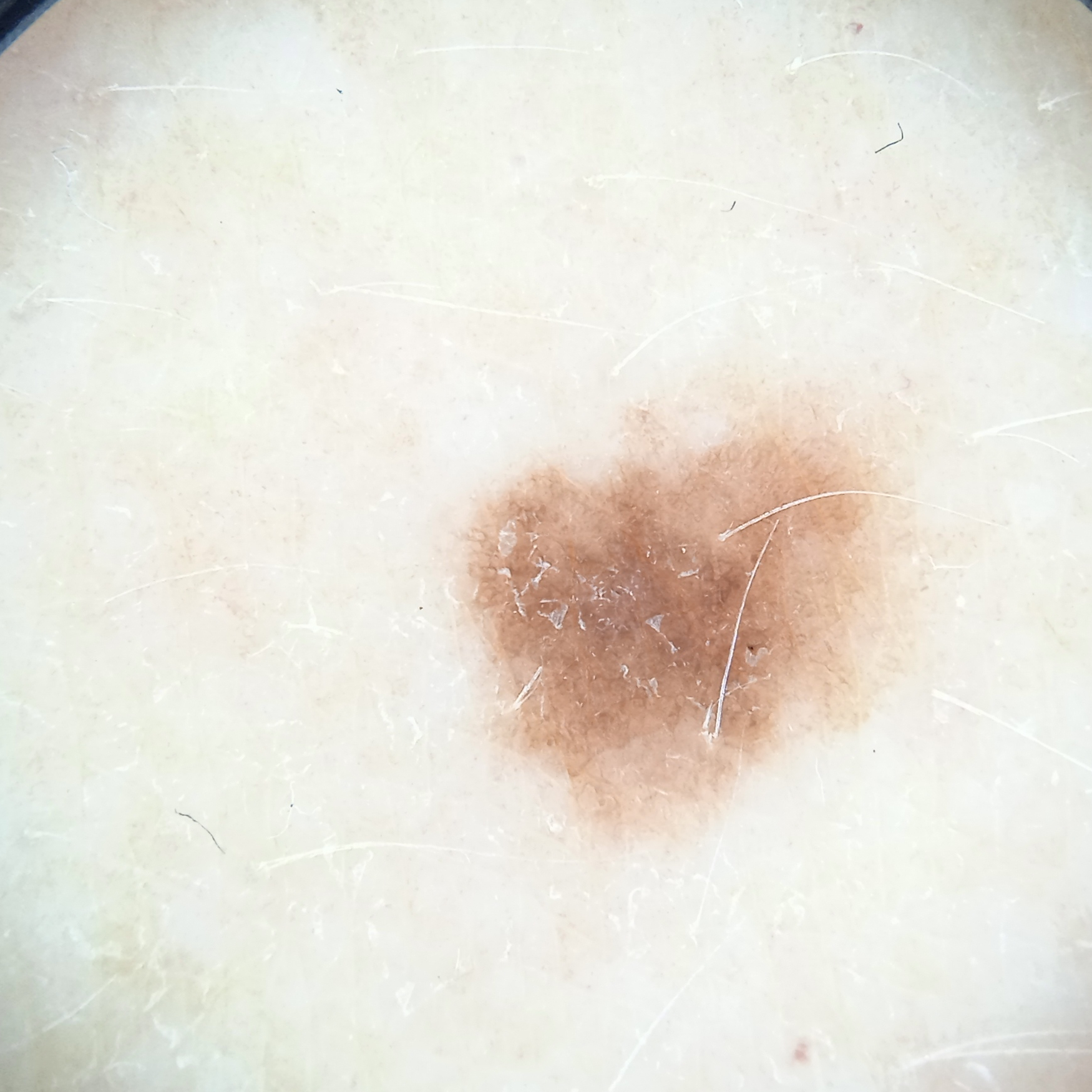Dermoscopy of a skin lesion.
Acquired for a research image collection, with no referral diagnosis.
A female patient age 50.
Located on the torso.
The lesion measures approximately 5.4 mm.
The diagnostic impression was a melanocytic nevus.